A dermoscopic photograph of a skin lesion.
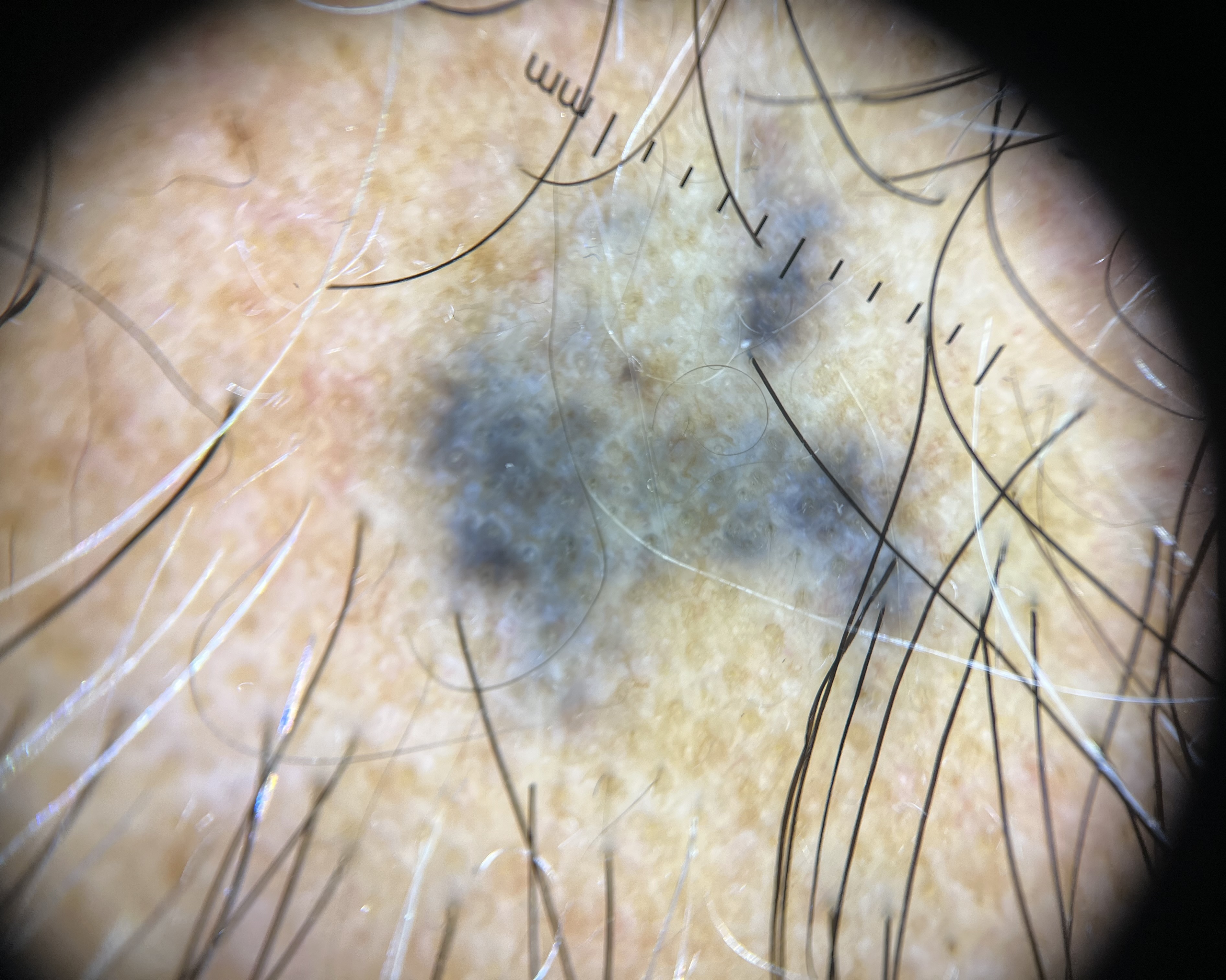assessment: blue nevus (expert consensus).